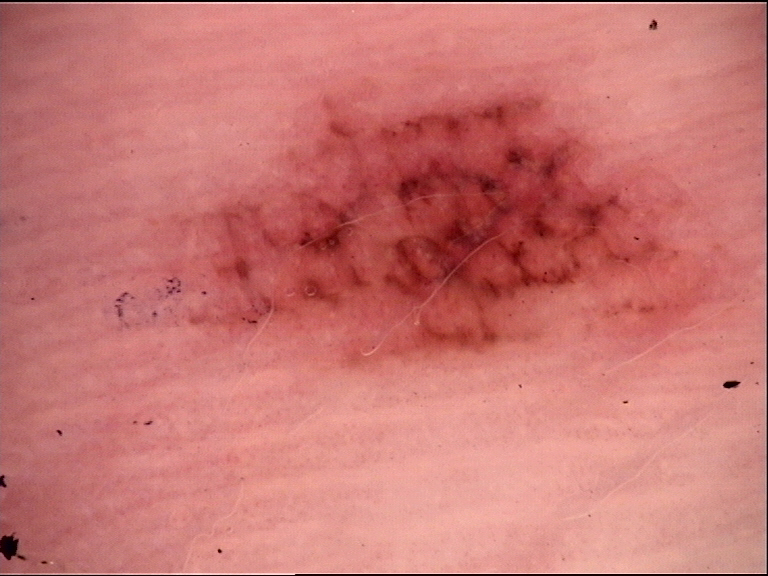A dermoscopic close-up of a skin lesion.
This is a banal lesion.
Diagnosed as an acral junctional nevus.